The patient considered this a rash · Fitzpatrick II; lay graders estimated 2 on the Monk Skin Tone · the patient reported no systemic symptoms · texture is reported as raised or bumpy · female subject, age 60–69 · reported duration is less than one week · the contributor reports itching · a close-up photograph · the affected area is the arm: 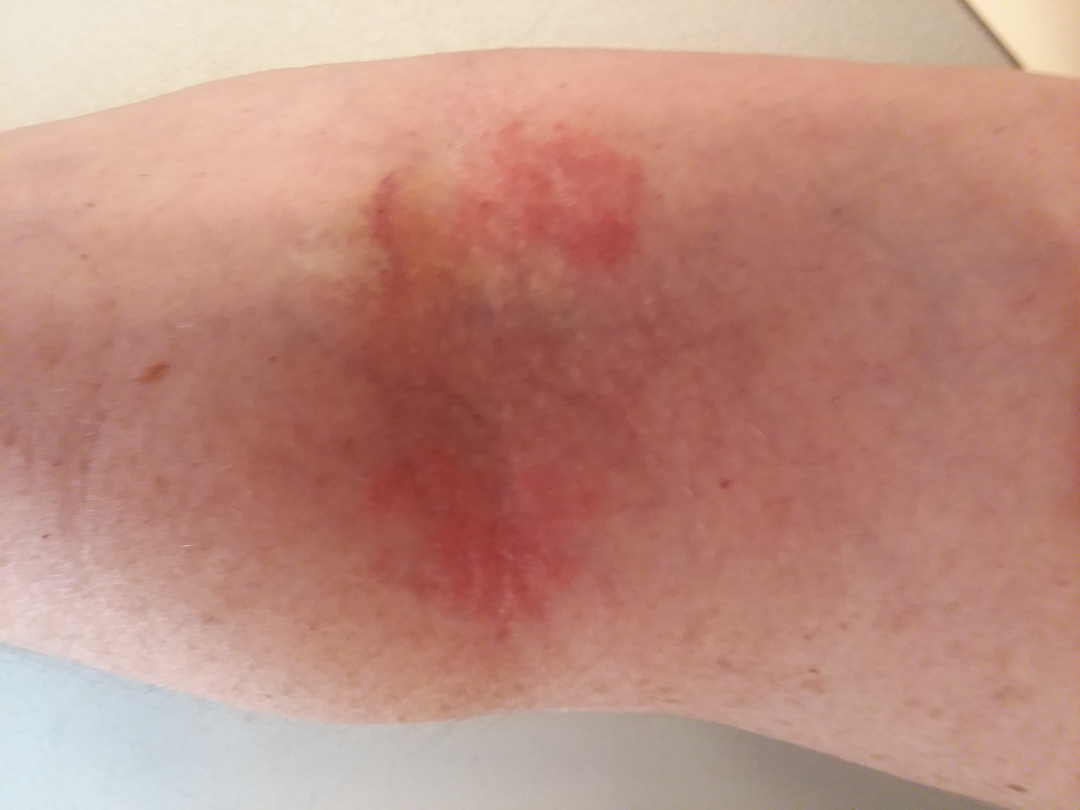No differential diagnosis could be assigned on photographic review.